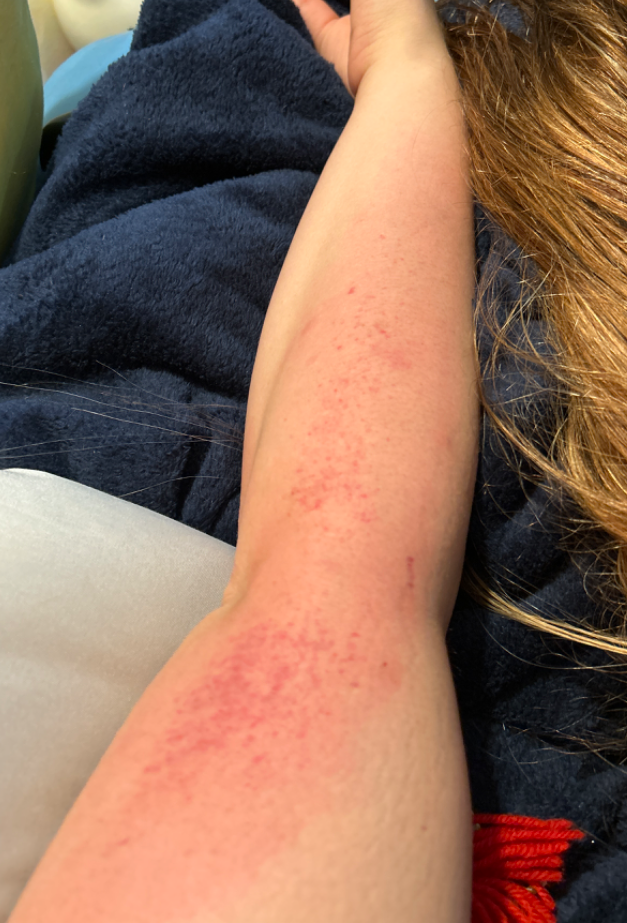The photograph is a close-up of the affected area. On dermatologist assessment of the image, most consistent with Eczema; possibly Allergic Contact Dermatitis.